A female patient 55 years old. By self-report, a prior organ transplant and immunosuppression. A moderate number of moles by the patient's own estimate: 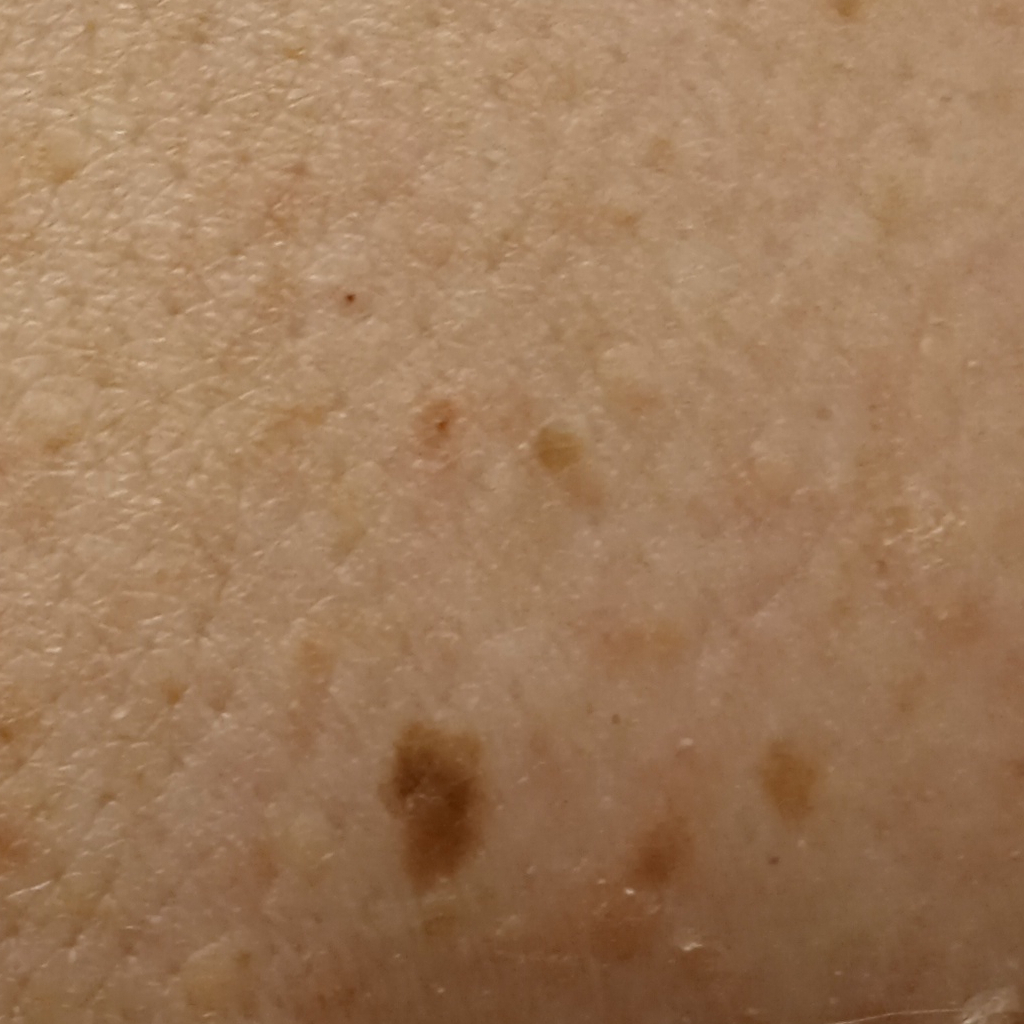| field | value |
|---|---|
| diagnostic label | melanocytic nevus (dermatologist consensus) |